A dermoscopic close-up of a skin lesion.
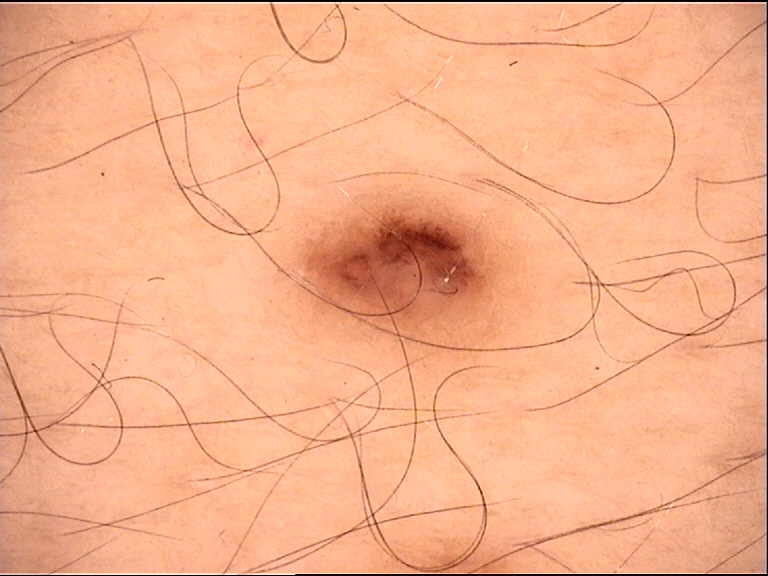| field | value |
|---|---|
| class | dysplastic junctional nevus (expert consensus) |